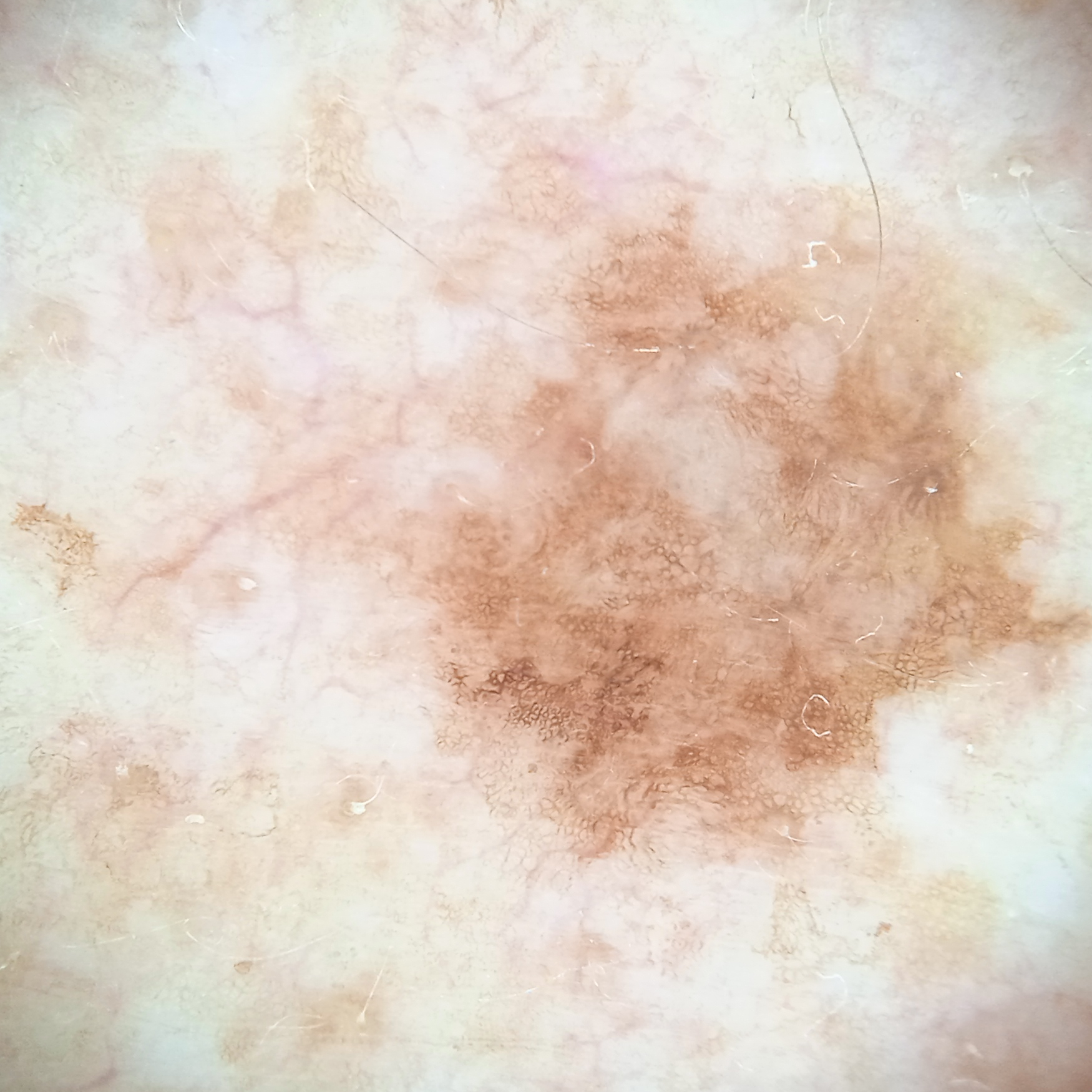The reviewing dermatologists could not reach a confident diagnosis. Case summary: The patient says their skin reddens with sun exposure. By self-report, a family history of skin cancer and a personal history of cancer. A dermoscopic image of a skin lesion. Few moles overall by the patient's own estimate. Imaged for a research study, with no referral diagnosis recorded. A male patient age 81. The lesion is on the back. Measuring roughly 8 mm.